A male subject age 65; a skin lesion imaged with a dermatoscope; imaged for a research study, with no referral diagnosis recorded — 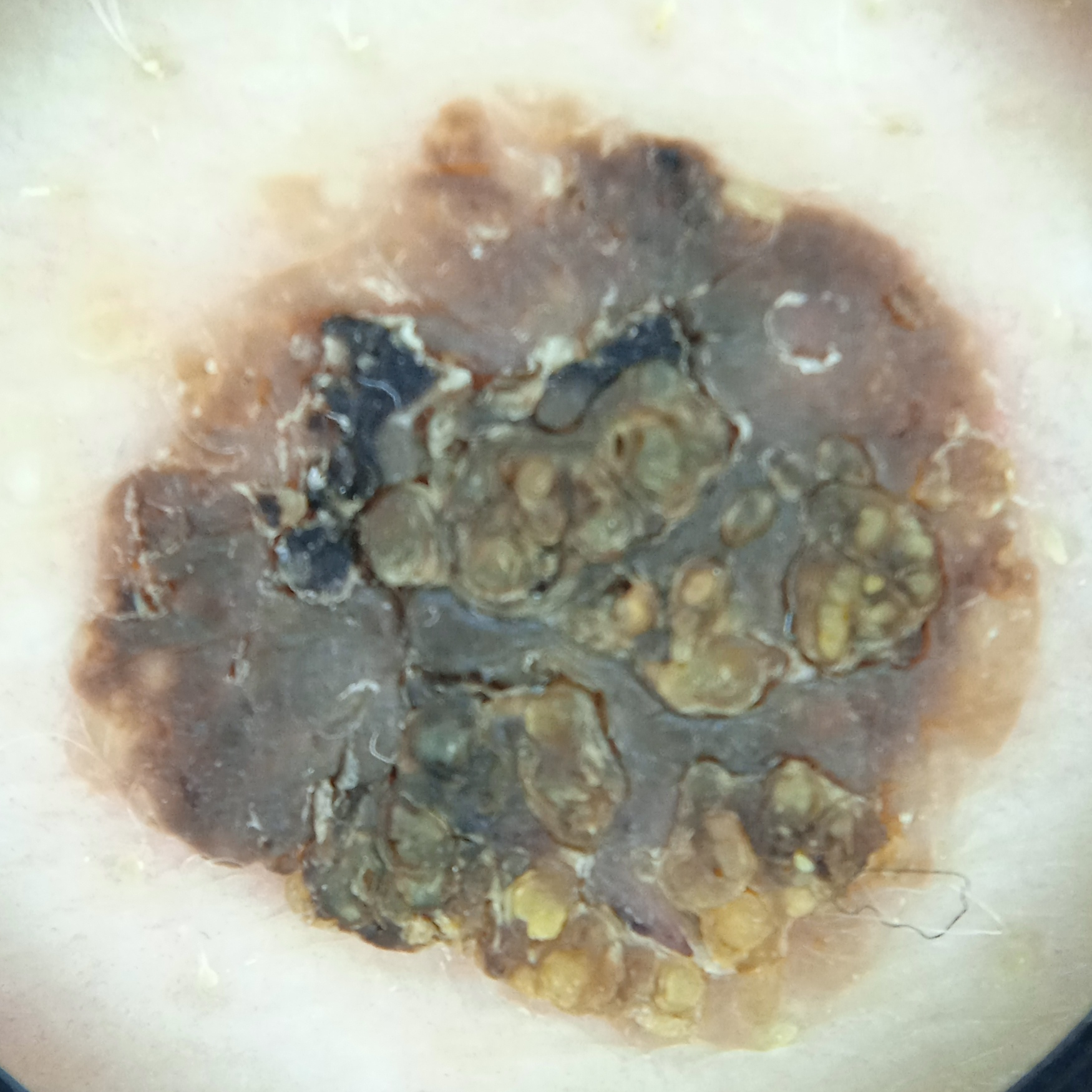Findings: The lesion is on the back. The lesion is about 12 mm across. Assessment: On independent review by four dermatologists, the agreed diagnosis was a seborrheic keratosis; the four reviewers were unanimous; the reviewers were fairly confident.